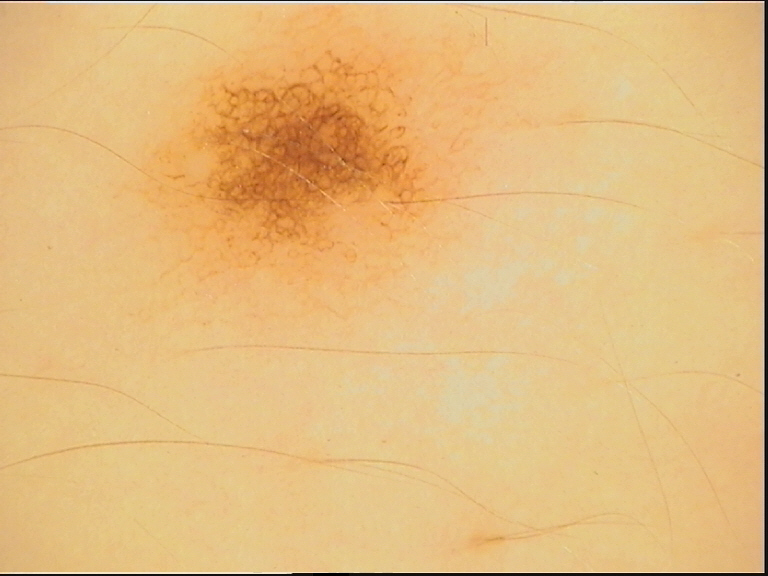Q: What is this lesion?
A: dysplastic junctional nevus (expert consensus)